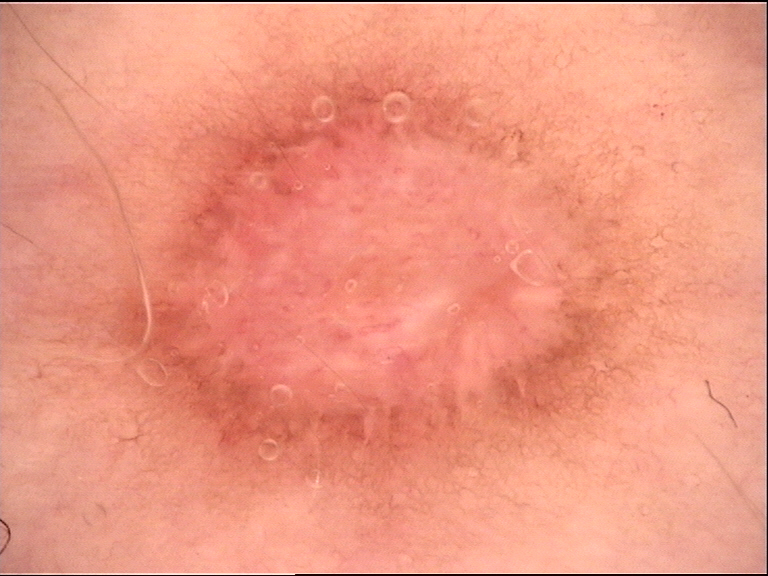Impression: Diagnosed as a dermal nevus.